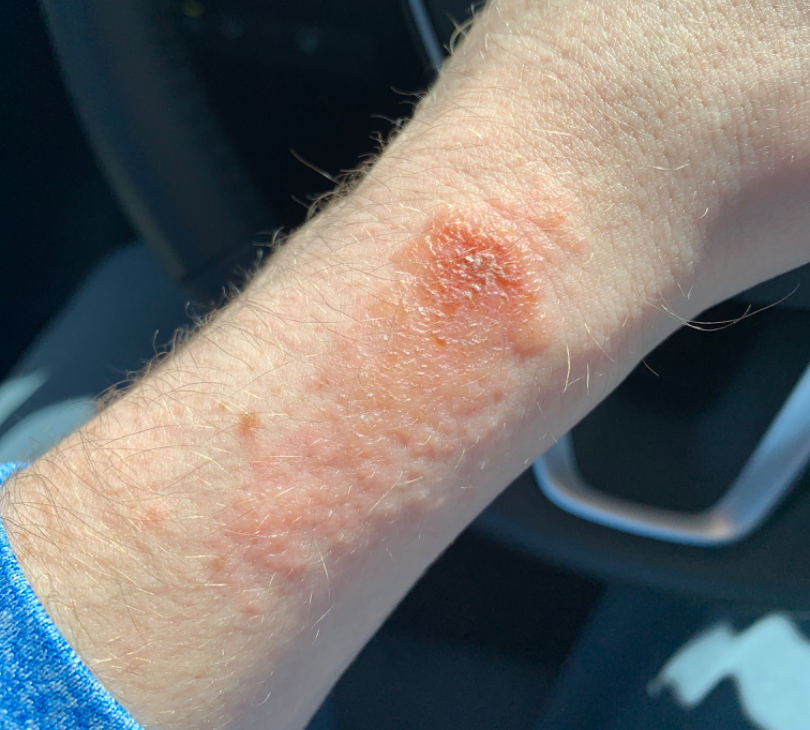Located on the leg, front of the torso, back of the hand, top or side of the foot and arm. A close-up photograph. On photographic review by a dermatologist, Allergic Contact Dermatitis (weight 1.00).